A dermoscopic photograph of a skin lesion.
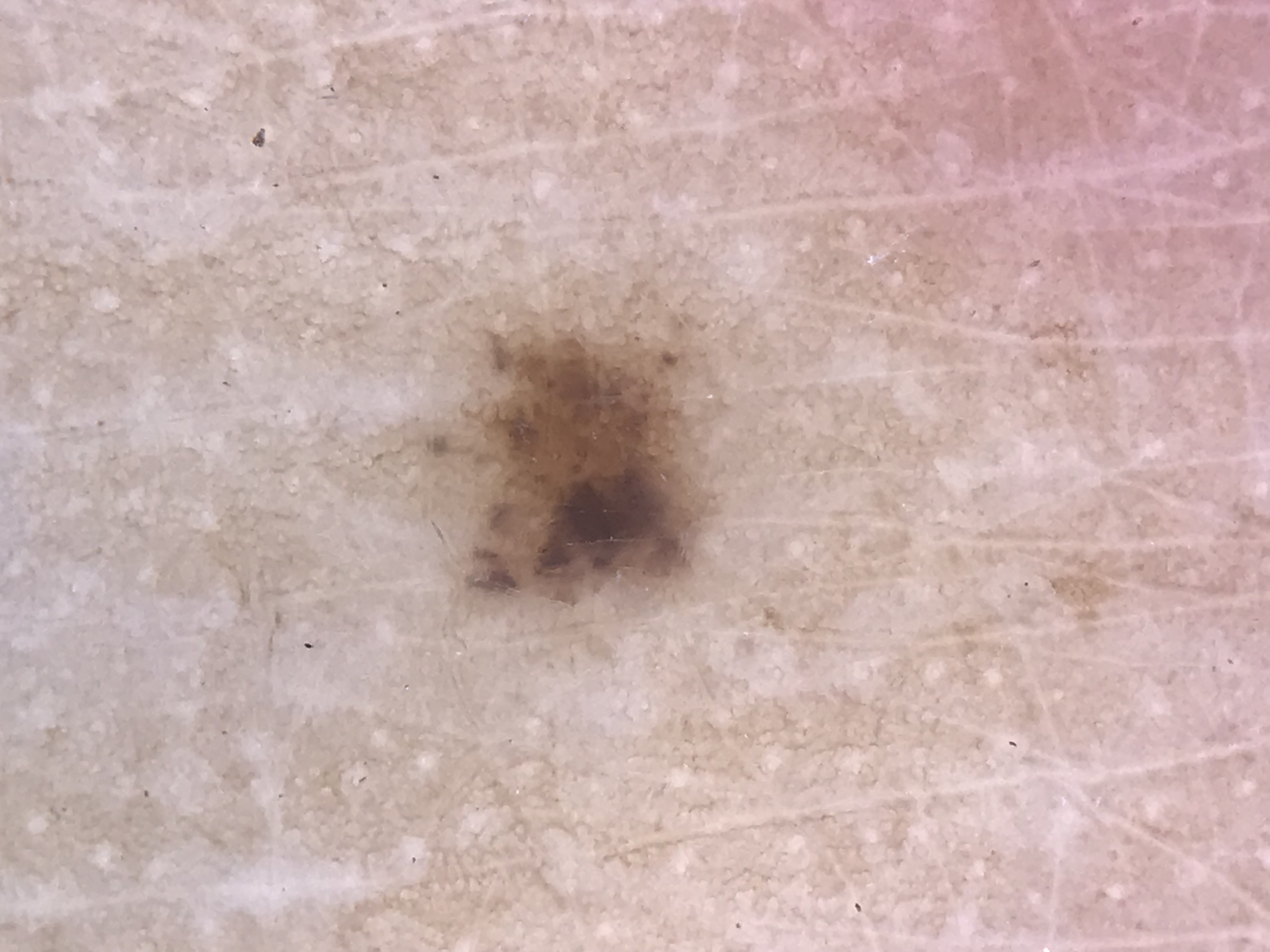Conclusion: Labeled as a dysplastic junctional nevus.